The photo was captured at an angle.
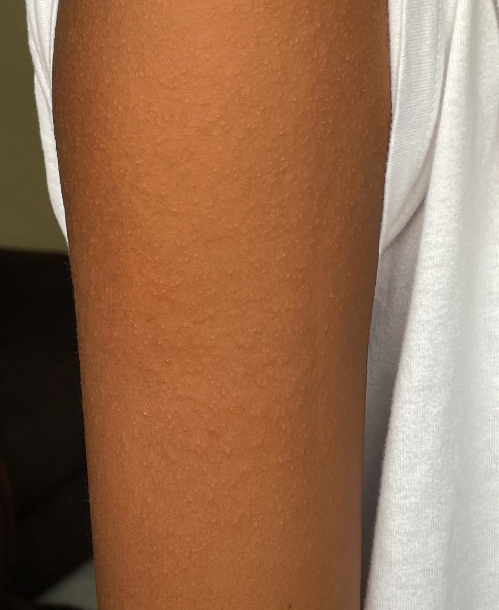Q: What was the assessment?
A: indeterminate from the photograph